The lesion is associated with enlargement, pain, bothersome appearance and itching. Present for less than one week. The patient indicates associated mouth sores. A close-up photograph. The subject is a female aged 50–59. The head or neck is involved. Skin tone: Fitzpatrick skin type II — 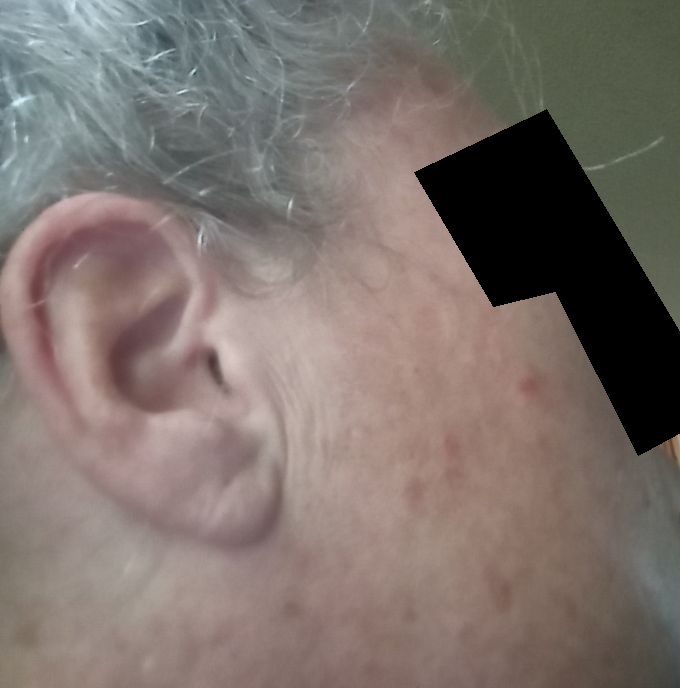{
  "differential": {
    "leading": [
      "Acne"
    ]
  }
}